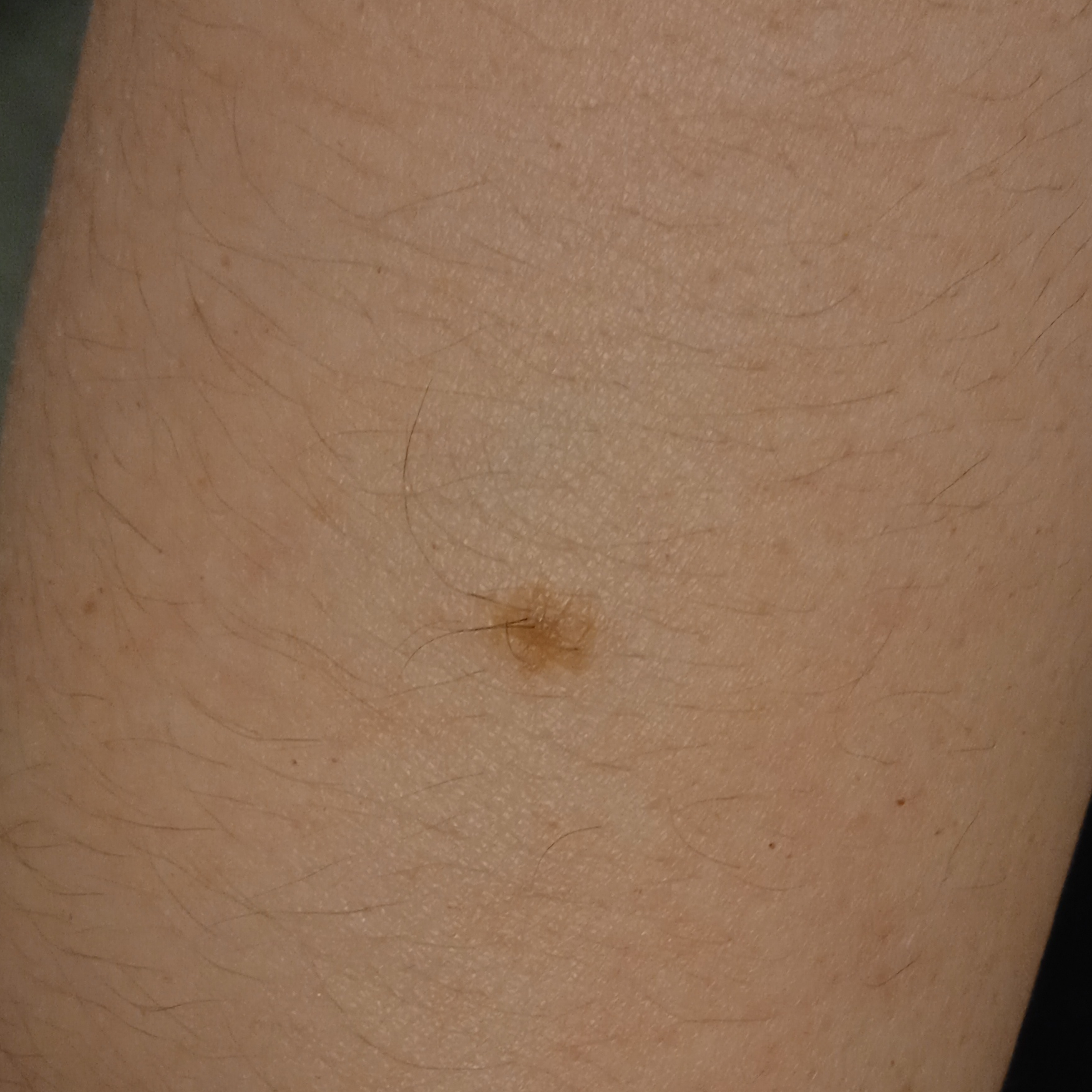| field | value |
|---|---|
| diagnostic label | melanocytic nevus (dermatologist consensus) |